A skin lesion imaged with a dermatoscope.
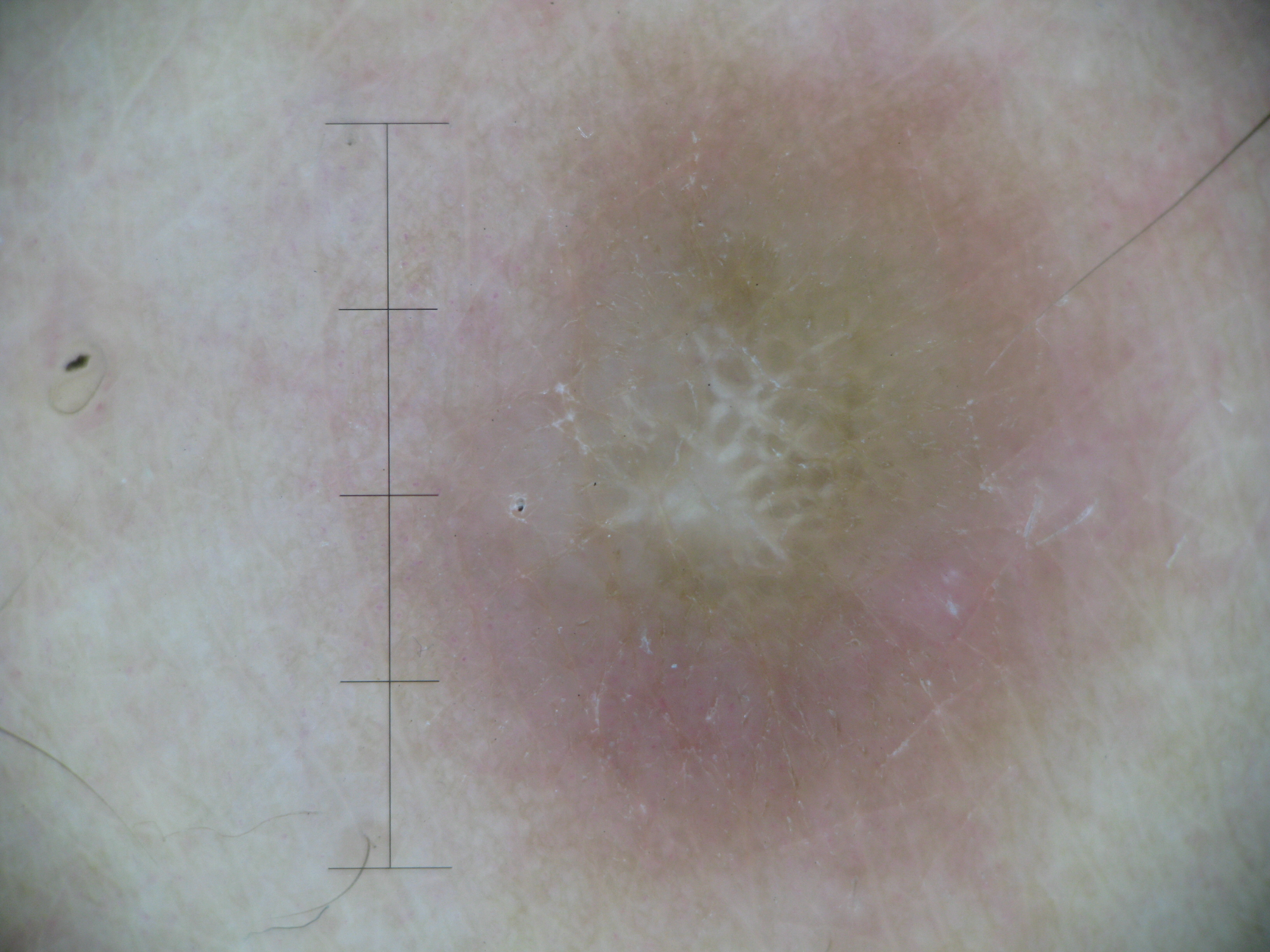The architecture is that of a fibro-histiocytic lesion. Diagnosed as a dermatofibroma.